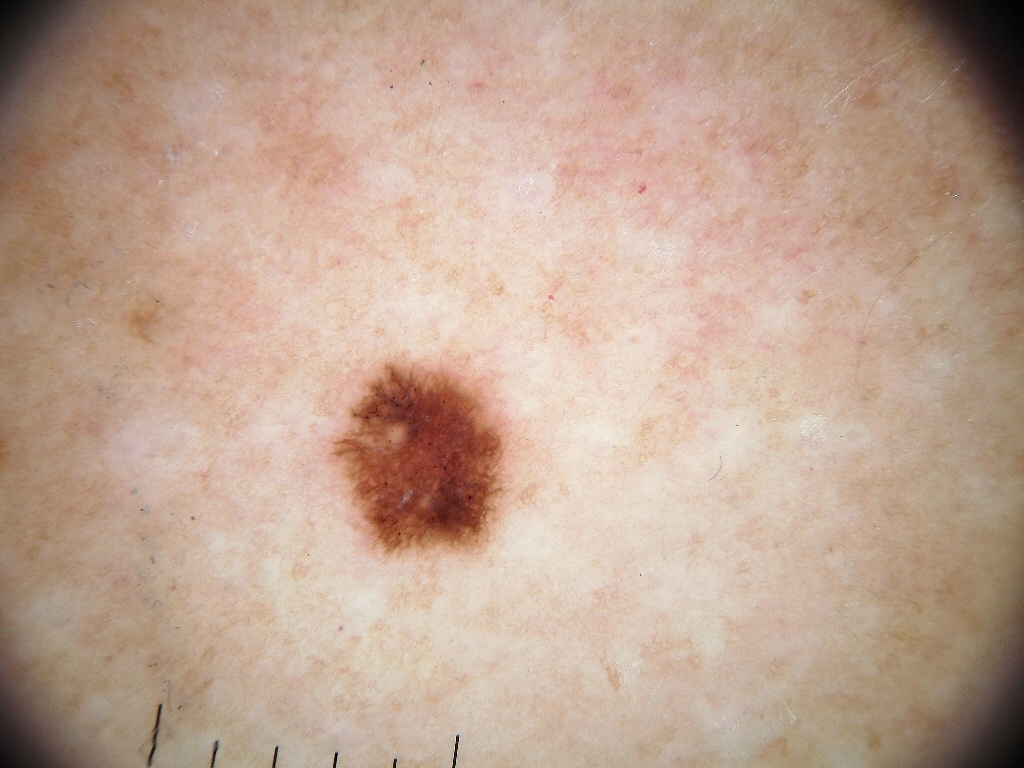Image and clinical context:
A female subject about 30 years old. This is a dermoscopic photograph of a skin lesion. The lesion's extent is left=323, top=358, right=508, bottom=555. Dermoscopic examination shows pigment network.
Impression:
The diagnostic assessment was a melanocytic nevus.